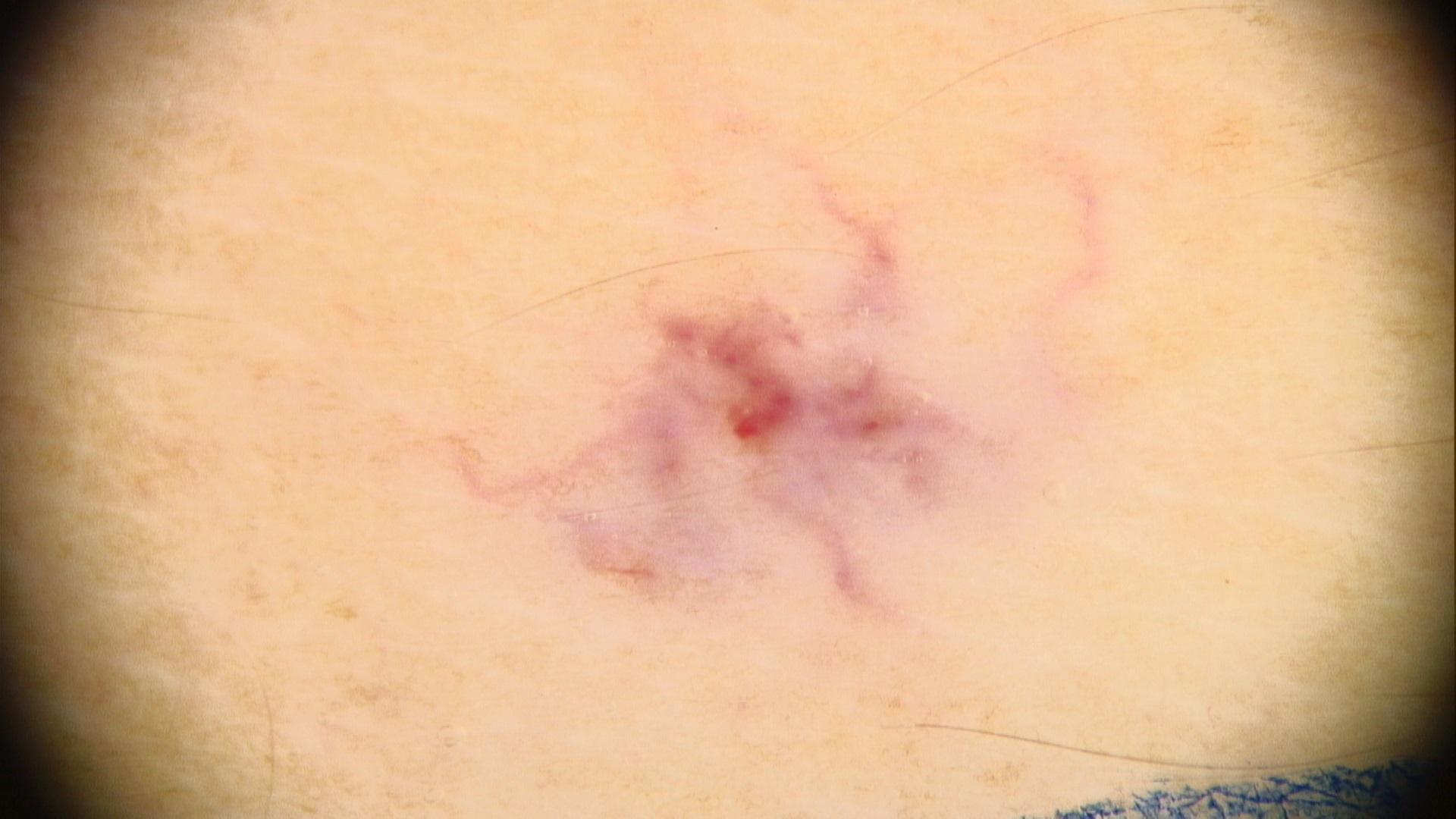Consistent with a vascular lesion.